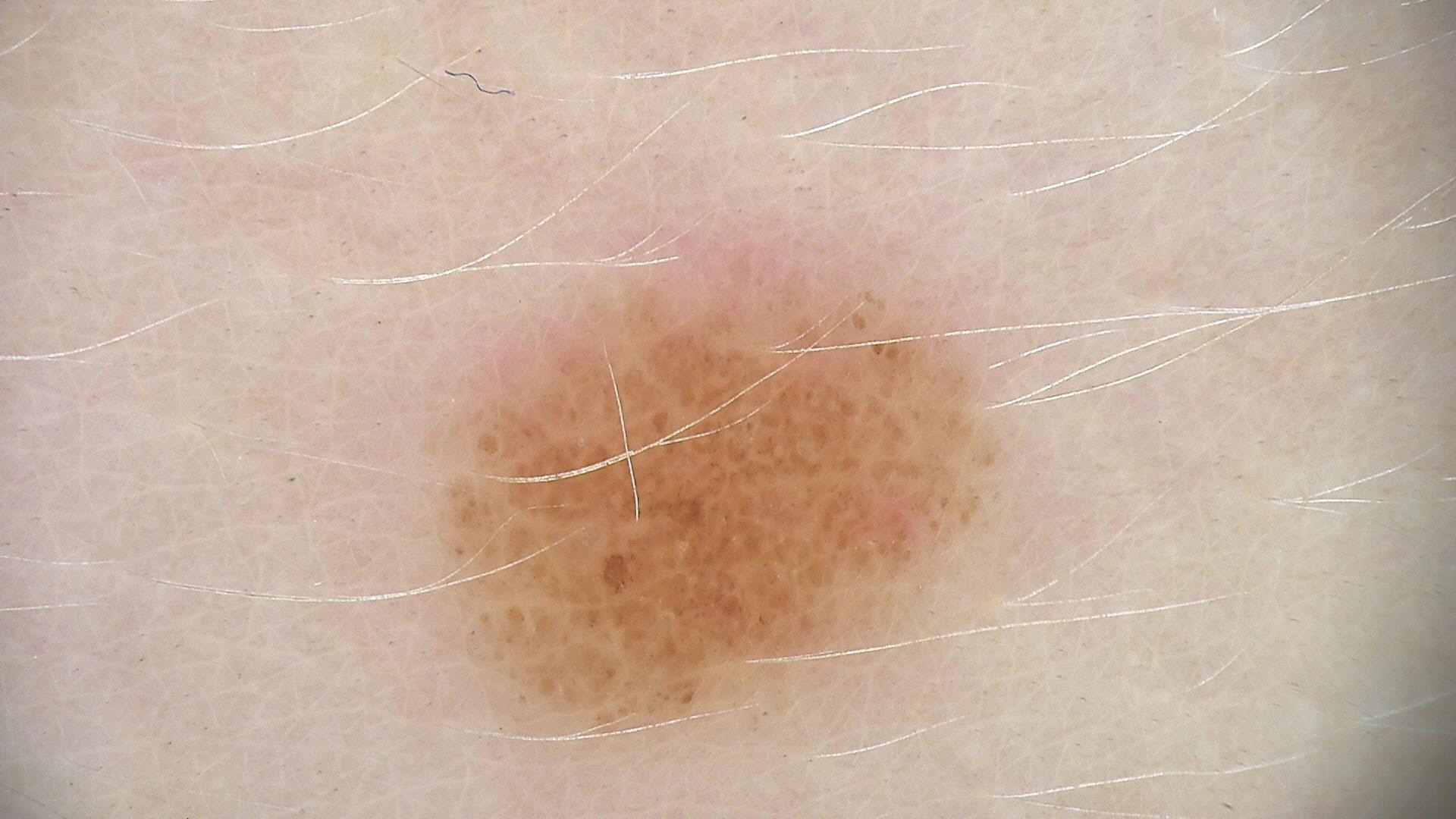Impression: Consistent with a dysplastic junctional nevus.